A dermoscopic photograph of a skin lesion.
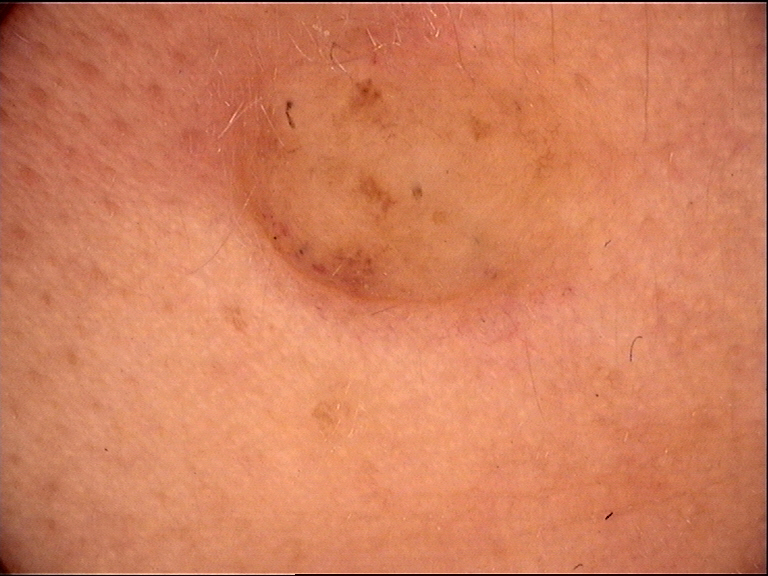The morphology is that of a banal lesion. Consistent with a dermal nevus.